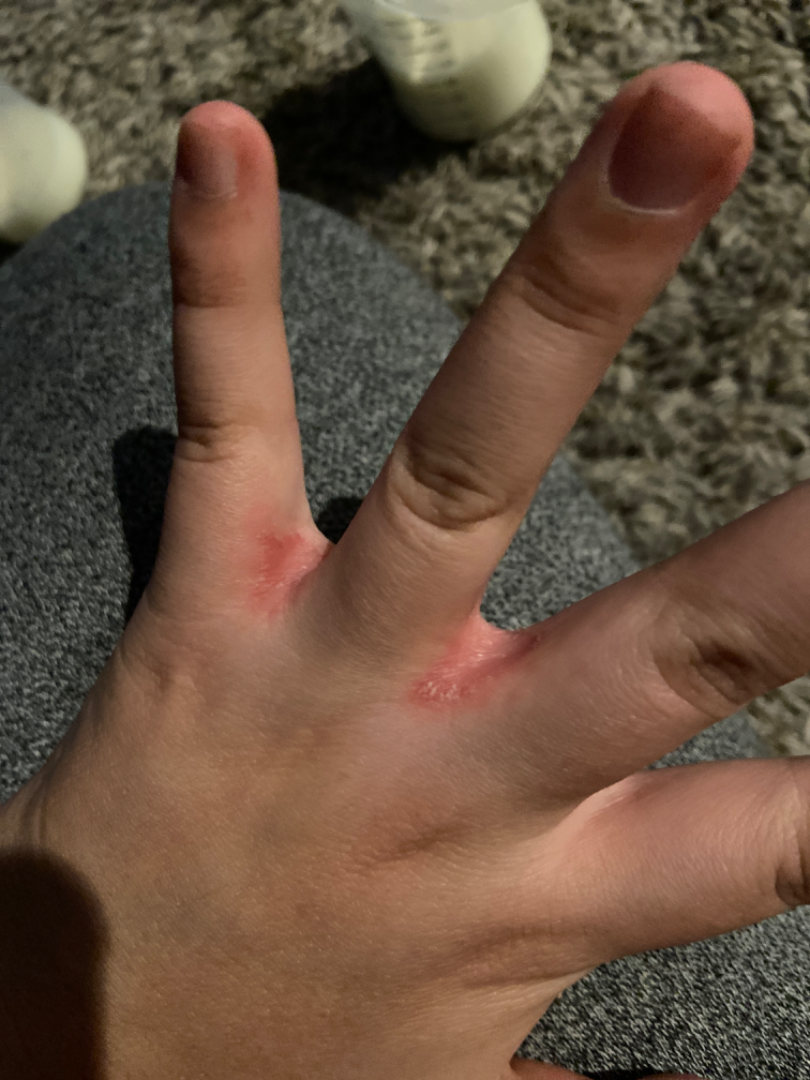| key | value |
|---|---|
| framing | at an angle |
| patient's own categorization | a rash |
| skin tone | FST III |
| patient-reported symptoms | itching, burning and bothersome appearance |
| body site | back of the hand |
| patient | female, age 18–29 |
| described texture | rough or flaky and flat |
| diagnostic considerations | single-reviewer assessment: the primary impression is Intertrigo; the differential also includes Psoriasis; less likely is Scabies |